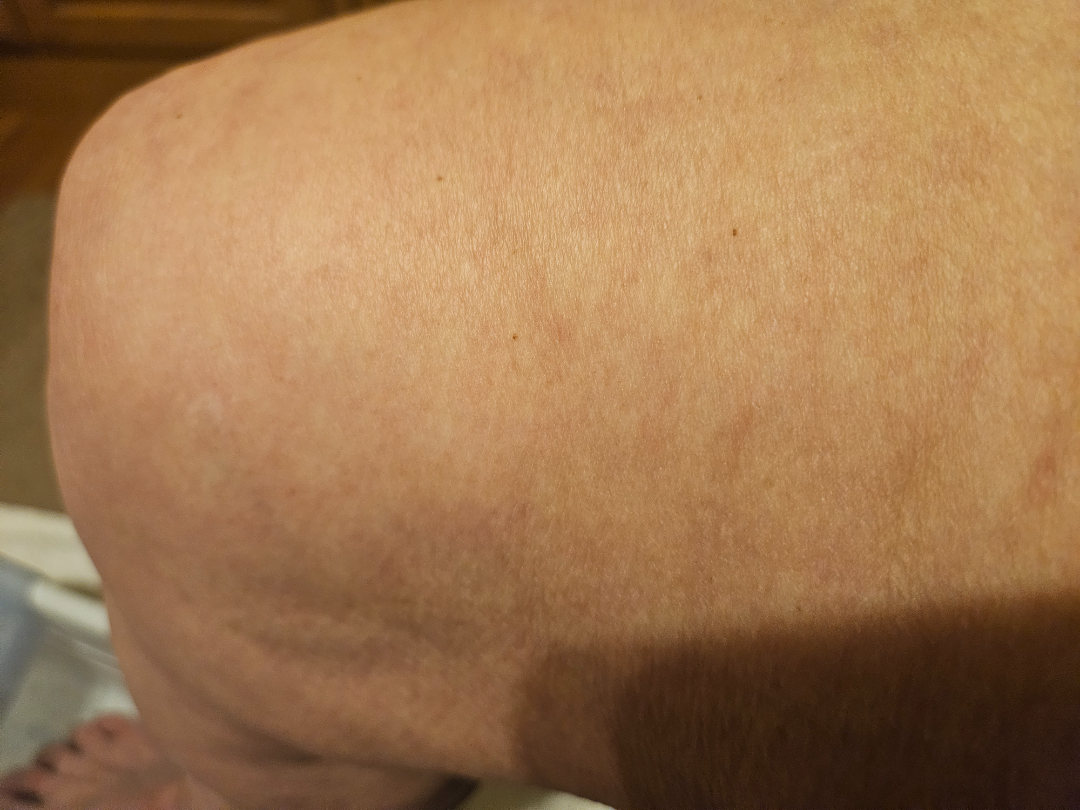No clear dermatological pathology was apparent in the photograph. An image taken at an angle. The affected area is the leg. The contributor is 70–79, female. Self-categorized by the patient as a rash. Symptoms reported: bothersome appearance. Present for one to three months. Texture is reported as flat.